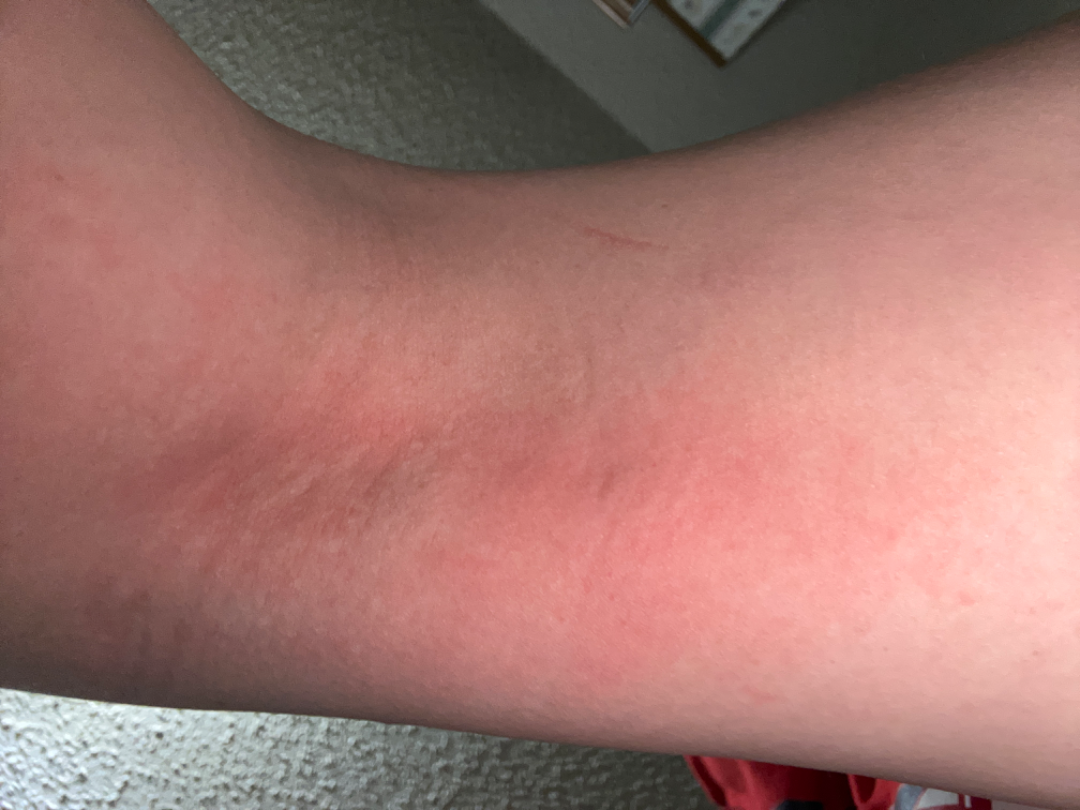The leg is involved.
Close-up view.
Texture is reported as raised or bumpy.
Present for less than one week.
On remote review of the image: Allergic Contact Dermatitis and Irritant Contact Dermatitis were each considered, in no particular order.